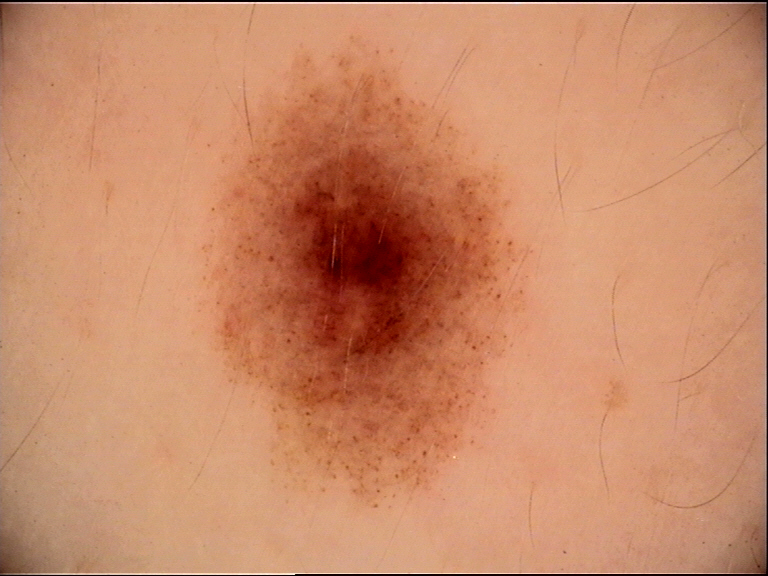image type: dermoscopy, diagnostic label: dysplastic compound nevus (expert consensus).